A skin lesion imaged with a dermatoscope: 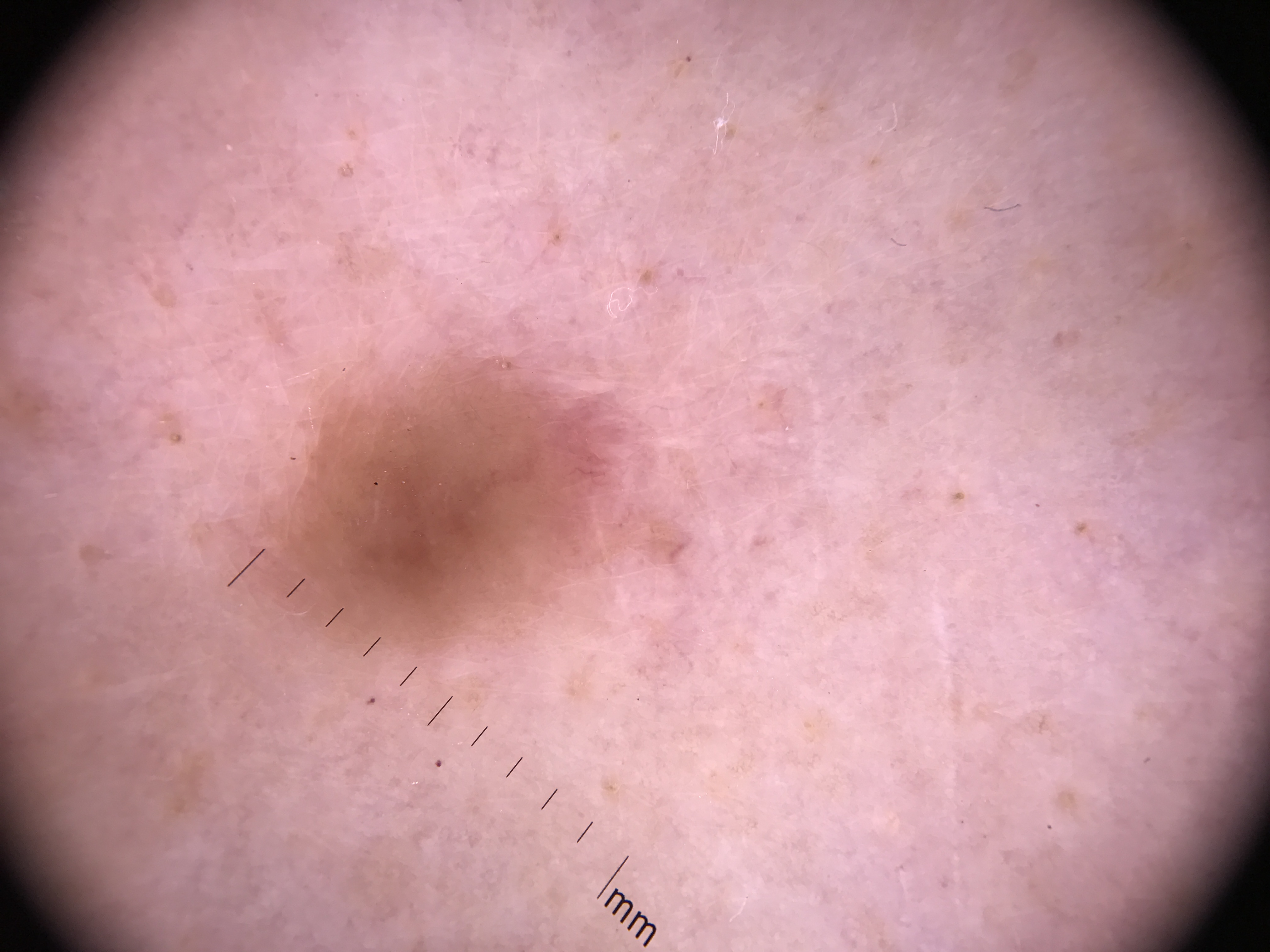label: dysplastic junctional nevus (expert consensus).